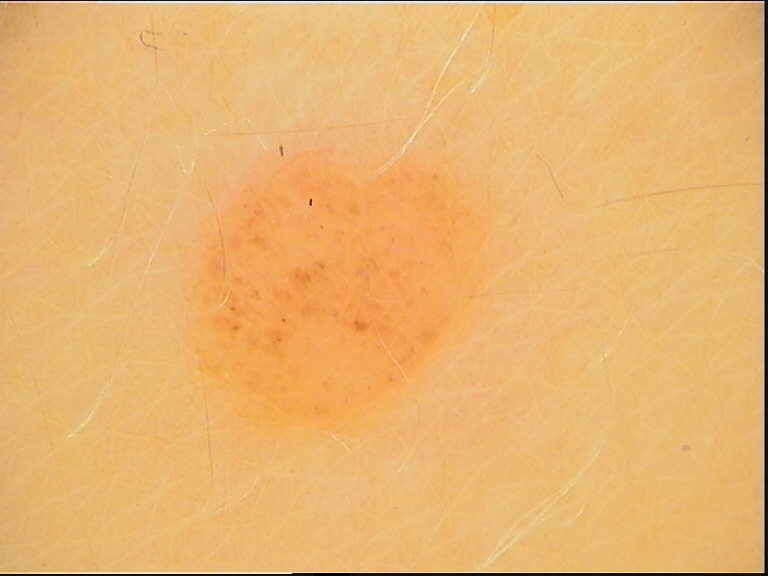image = dermoscopy
diagnosis = compound nevus (expert consensus)